The condition has been present for one to four weeks · the subject is a female aged 40–49 · located on the arm and head or neck · the contributor reports associated fatigue and shortness of breath · texture is reported as raised or bumpy · this image was taken at a distance: 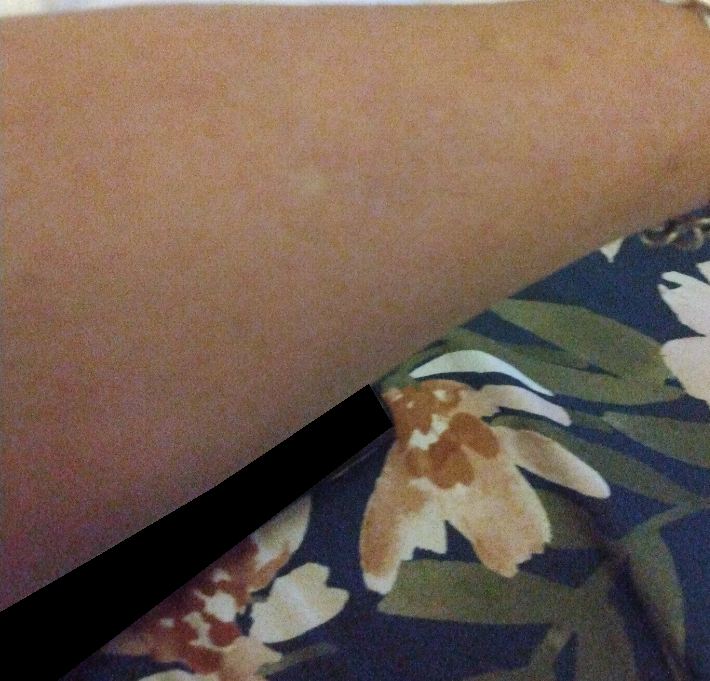| field | value |
|---|---|
| assessment | could not be assessed |